The contributor is male. The affected area is the arm. This image was taken at a distance: 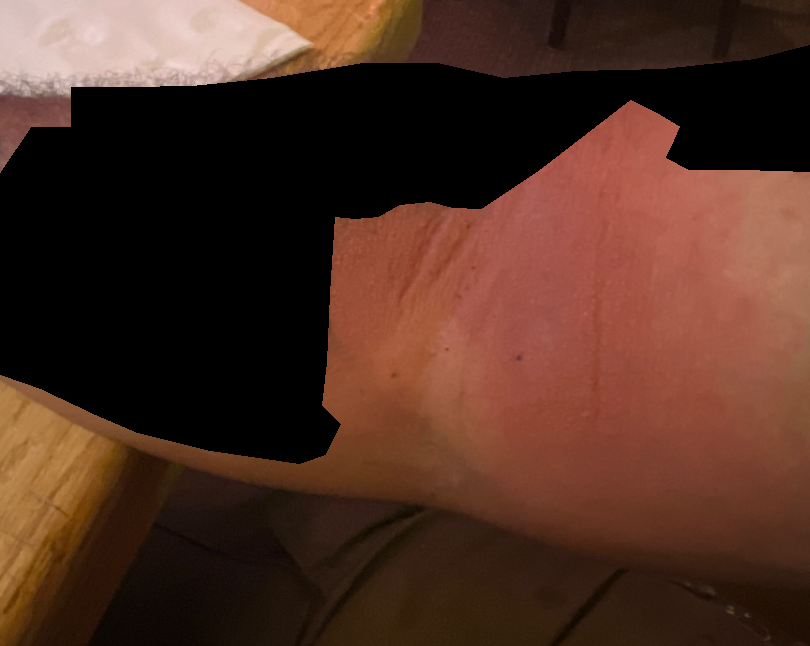On dermatologist assessment of the image: Cellulitis (possible); Eczema (possible); Allergic Contact Dermatitis (possible).